The leg is involved. This is a close-up image: 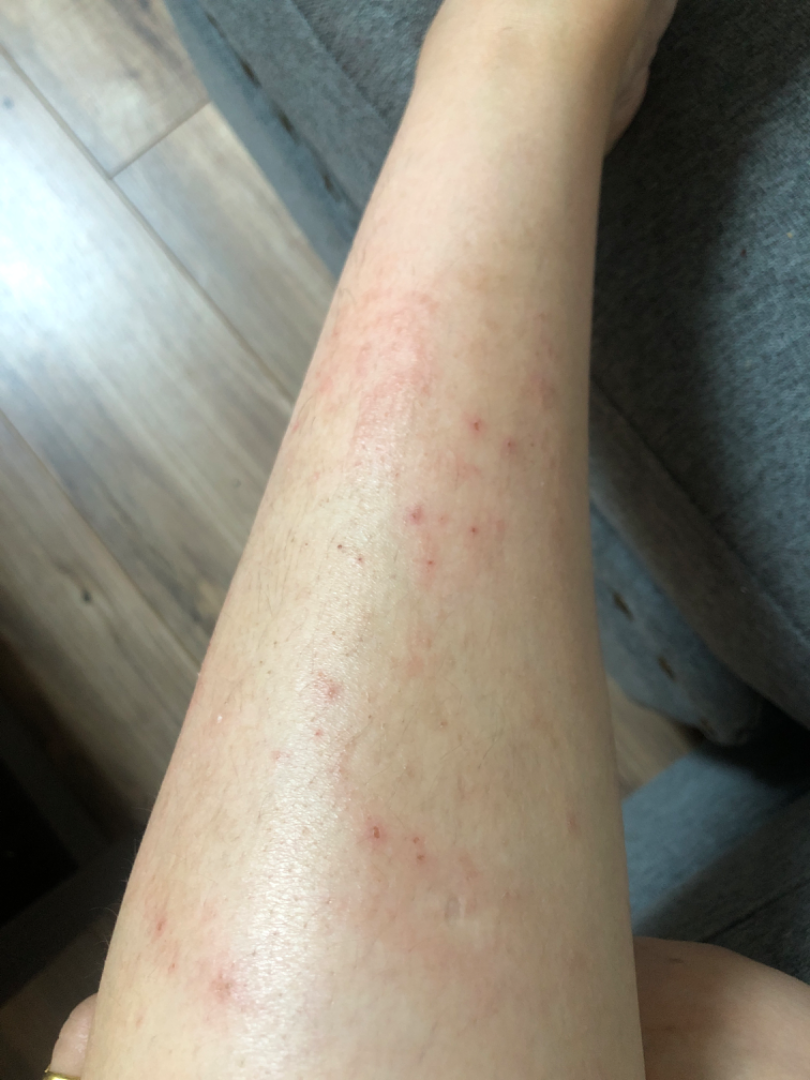skin tone = Fitzpatrick I; lay reviewers estimated MST 2–3
lesion texture = rough or flaky
present for = more than one year
differential diagnosis = Scabies, Eczema and Allergic Contact Dermatitis were each considered, in no particular order